This image was taken at a distance; the affected area is the front of the torso, back of the torso, arm and leg: 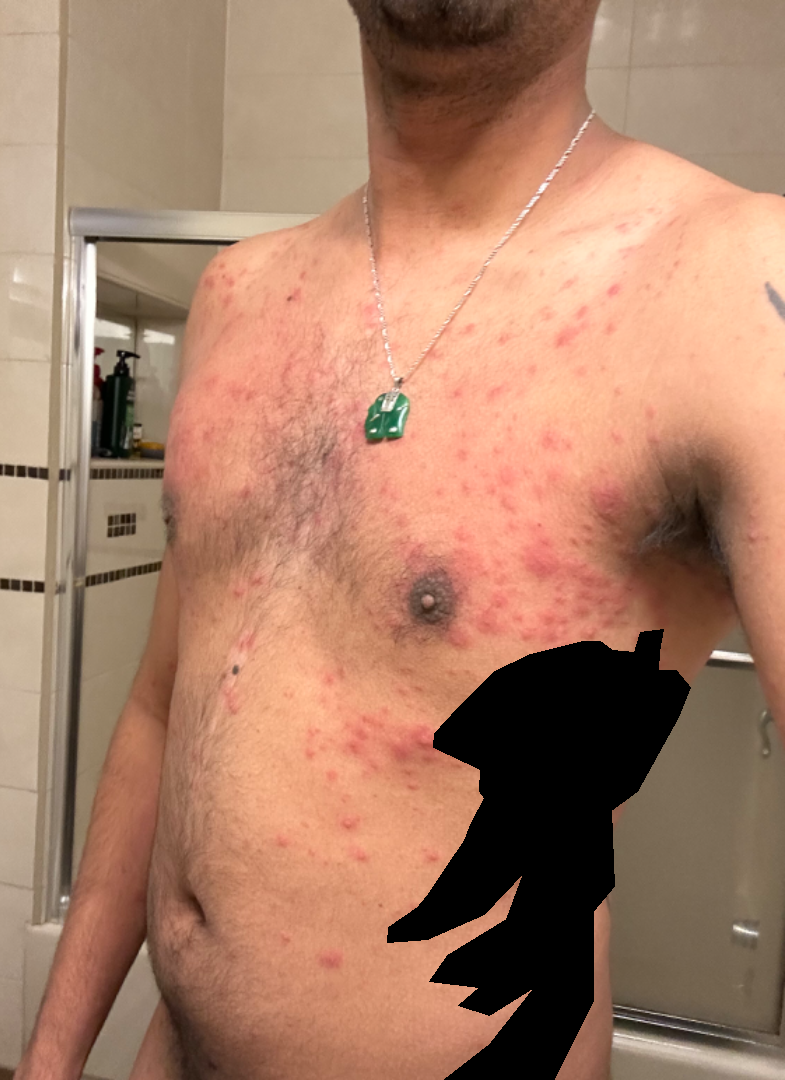differential:
  leading:
    - Drug Rash
  unlikely:
    - Viral Exanthem
    - Scabies
    - Folliculitis
    - Allergic Contact Dermatitis